A female patient aged 53-57; Fitzpatrick skin type II; a dermoscopic photograph of a skin lesion: 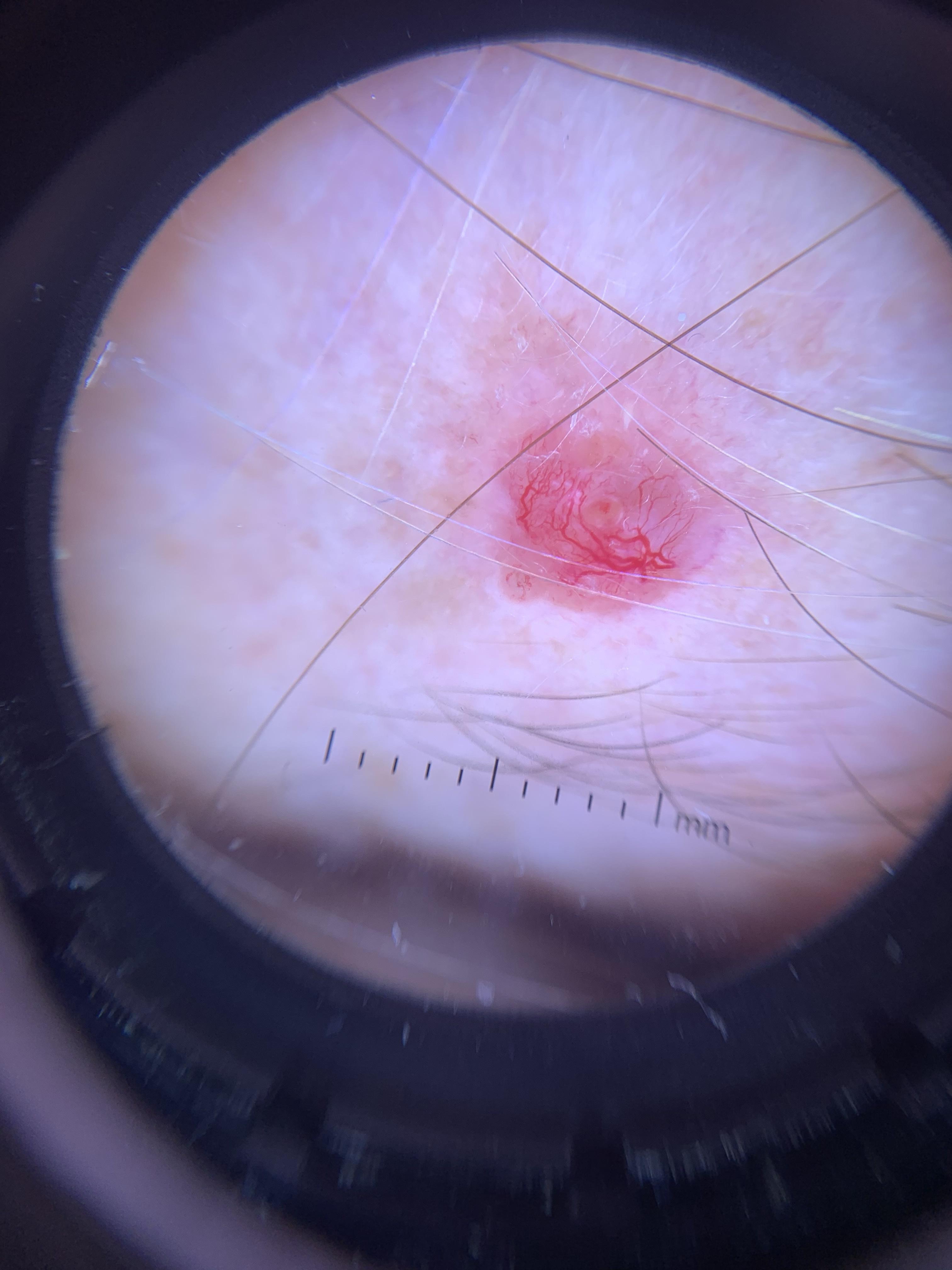The lesion was found on the head or neck. The biopsy diagnosis was a basal cell carcinoma.